A dermatoscopic image of a skin lesion:
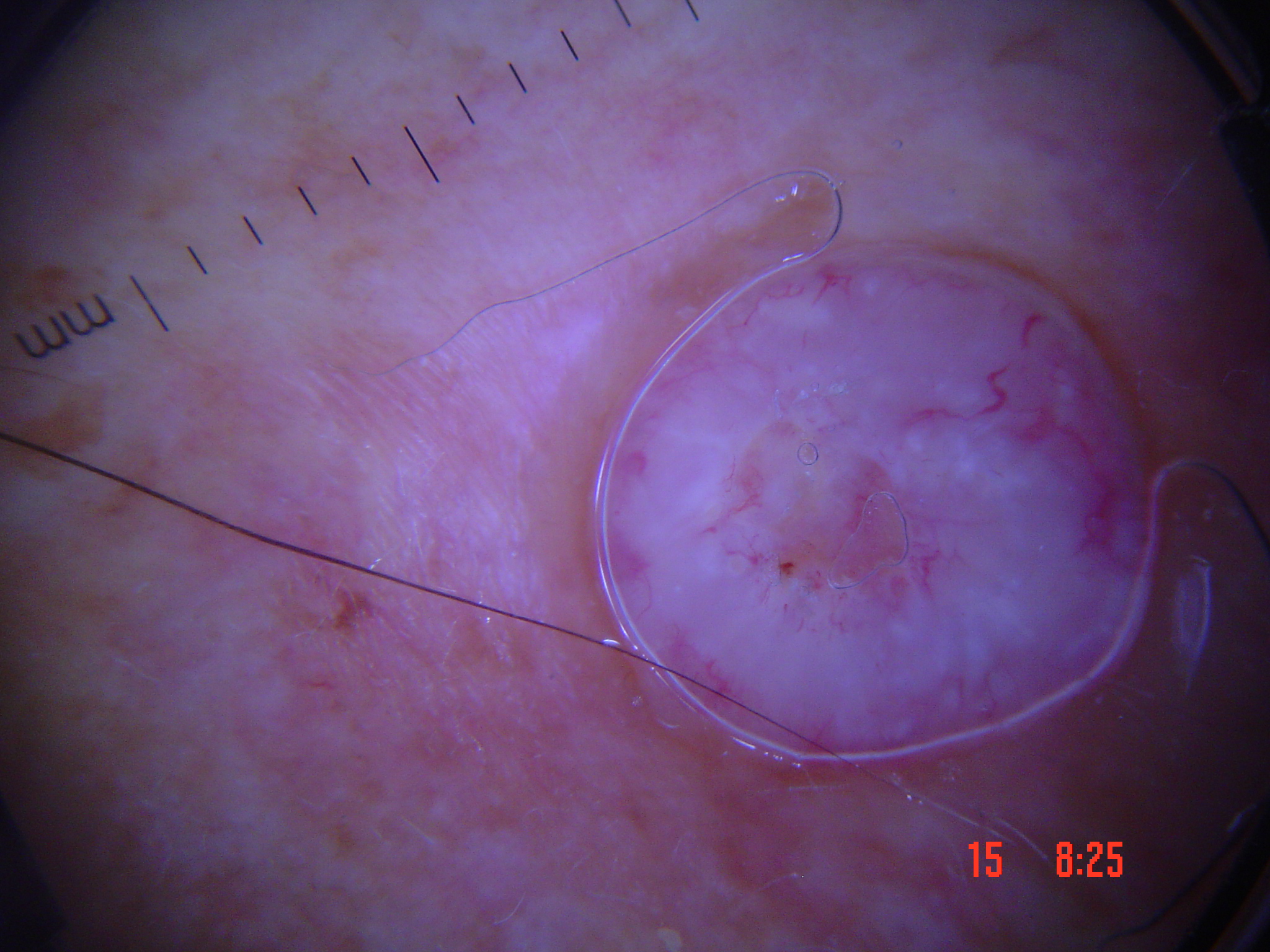subtype = keratinocytic, class = squamous cell carcinoma (biopsy-proven).